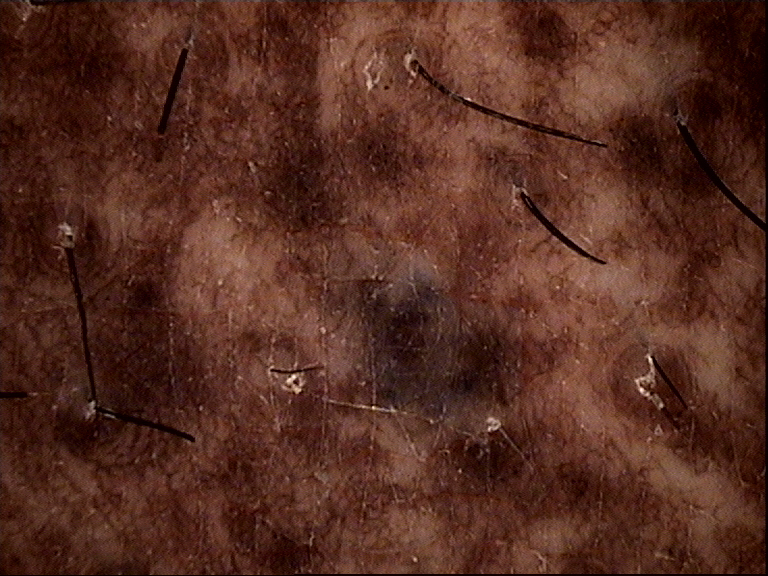image: dermoscopy
diagnosis:
  name: congenital compound nevus
  code: ccb
  malignancy: benign
  super_class: melanocytic
  confirmation: expert consensus